On a questionnaire the patient reported a history of sunbed use and a family history of skin cancer. The patient says their skin reddens painfully with sun exposure:
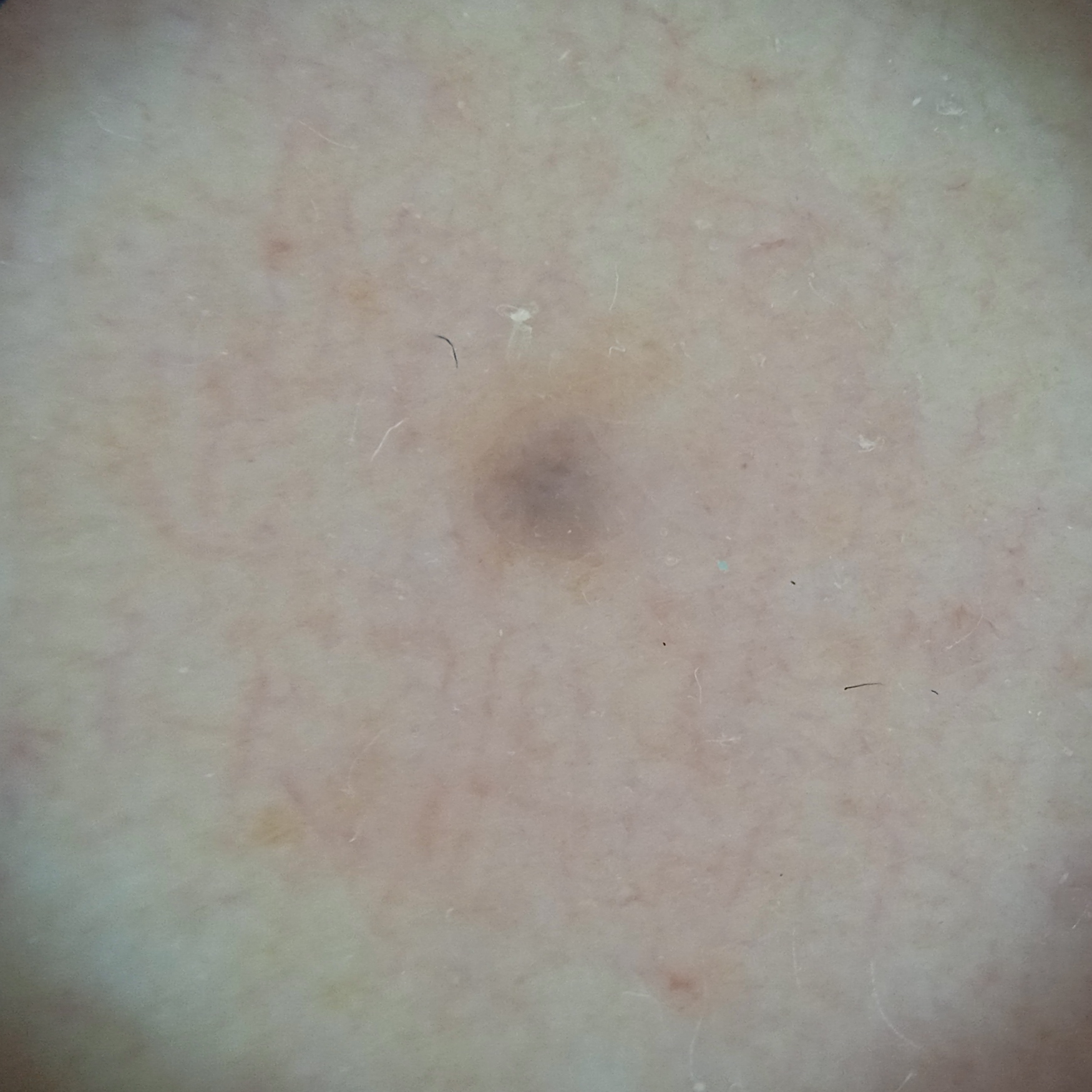The lesion is located on an arm.
Measuring roughly 1.8 mm.
The diagnostic impression was a melanocytic nevus.